Close-up view; the affected area is the arm — 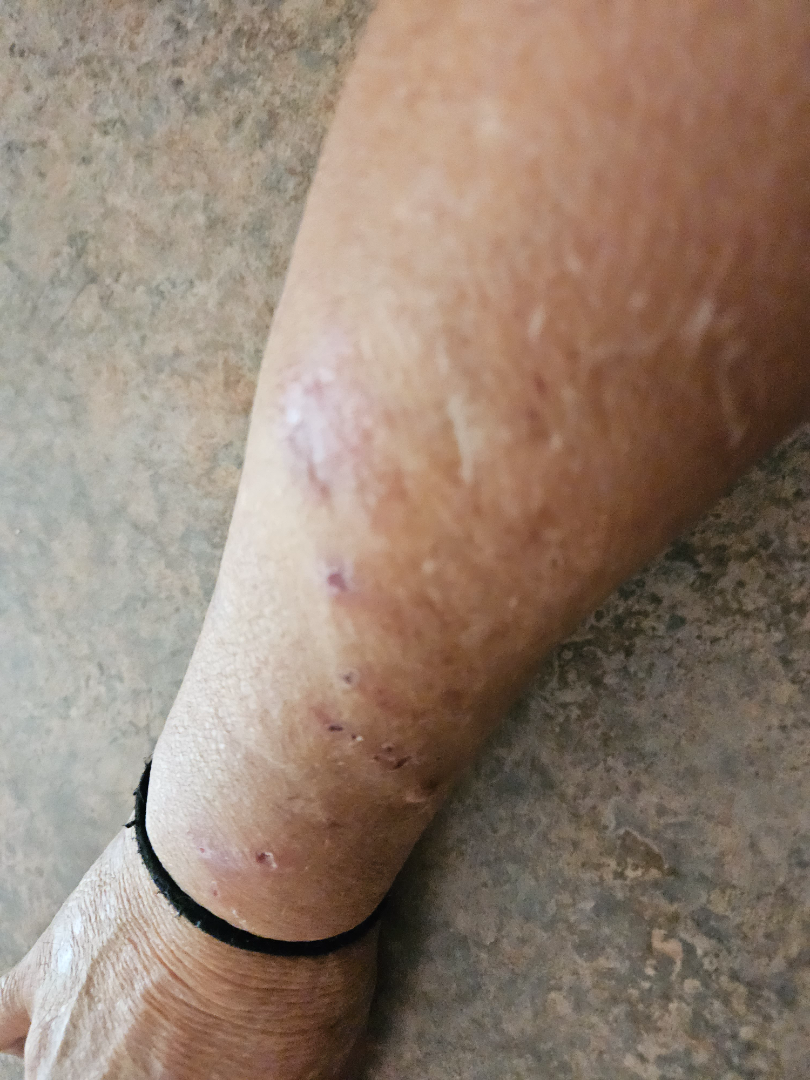assessment: unable to determine | symptoms: bothersome appearance, itching and bleeding | systemic symptoms: shortness of breath and joint pain | onset: one to four weeks | patient's own categorization: a rash | described texture: rough or flaky, raised or bumpy and fluid-filled.